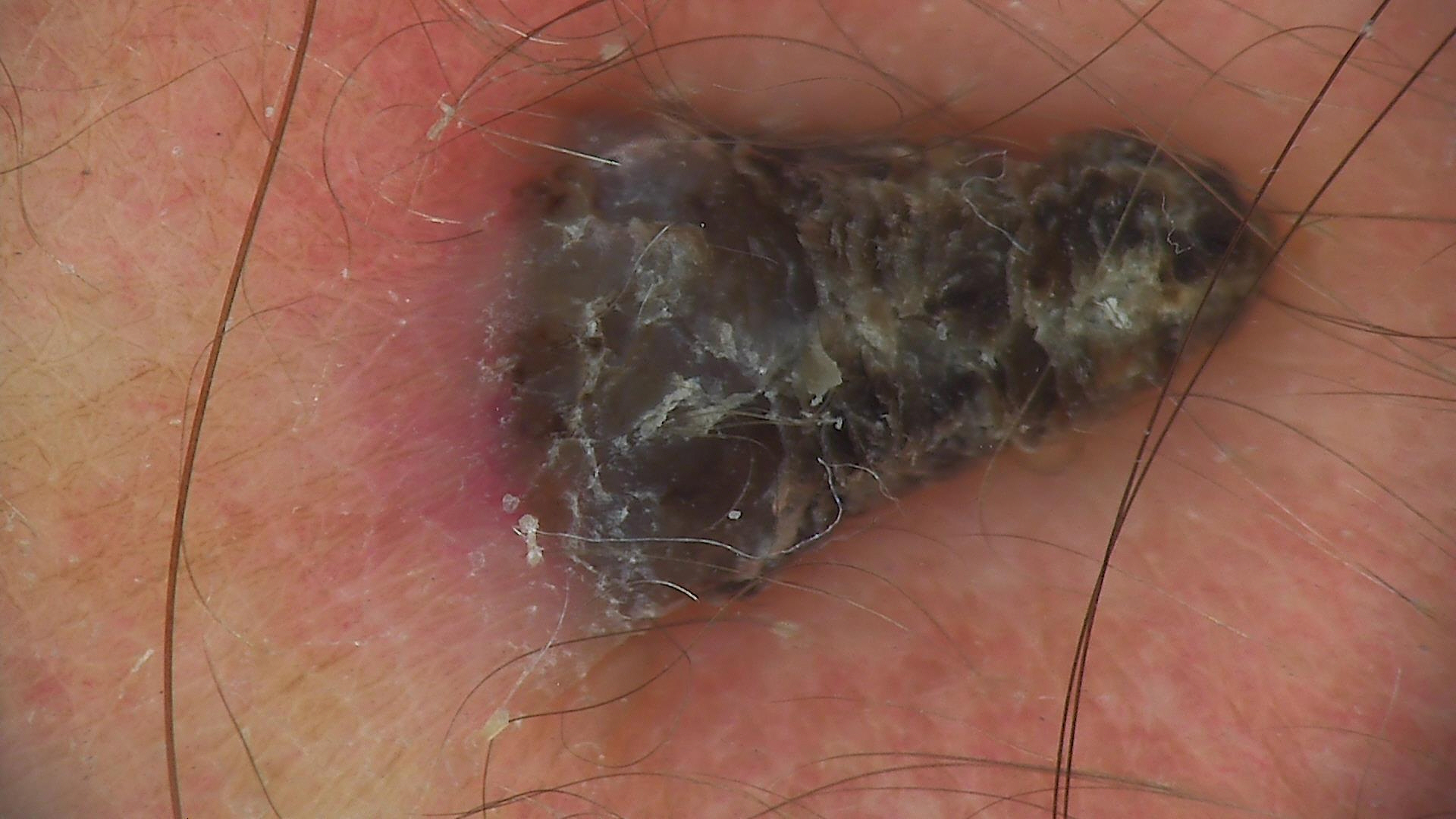- image · dermoscopy
- lesion type · keratinocytic
- class · cutaneous horn (biopsy-proven)